The affected area is the leg, the photo was captured at an angle, the patient is male: 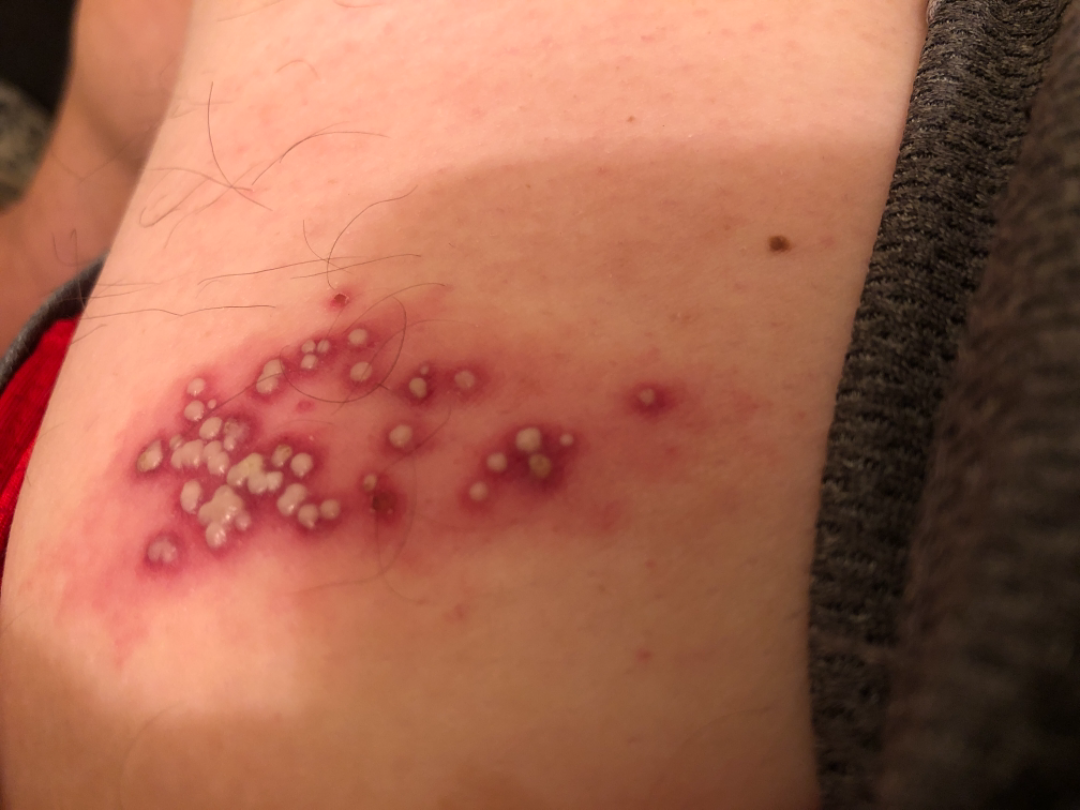Symptoms reported: darkening, pain, bothersome appearance, itching and burning. Non-clinician graders estimated MST 3 (US pool) or 2 (India pool). The lesion is described as raised or bumpy. The patient reports the condition has been present for less than one week. The patient described the issue as a rash. Single-reviewer assessment: the leading impression is Herpes Simplex; also on the differential is Herpes Zoster; less likely is Psoriasis.